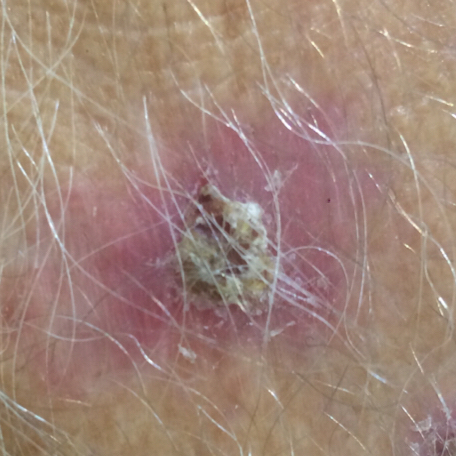Confirmed on histopathology as a basal cell carcinoma.